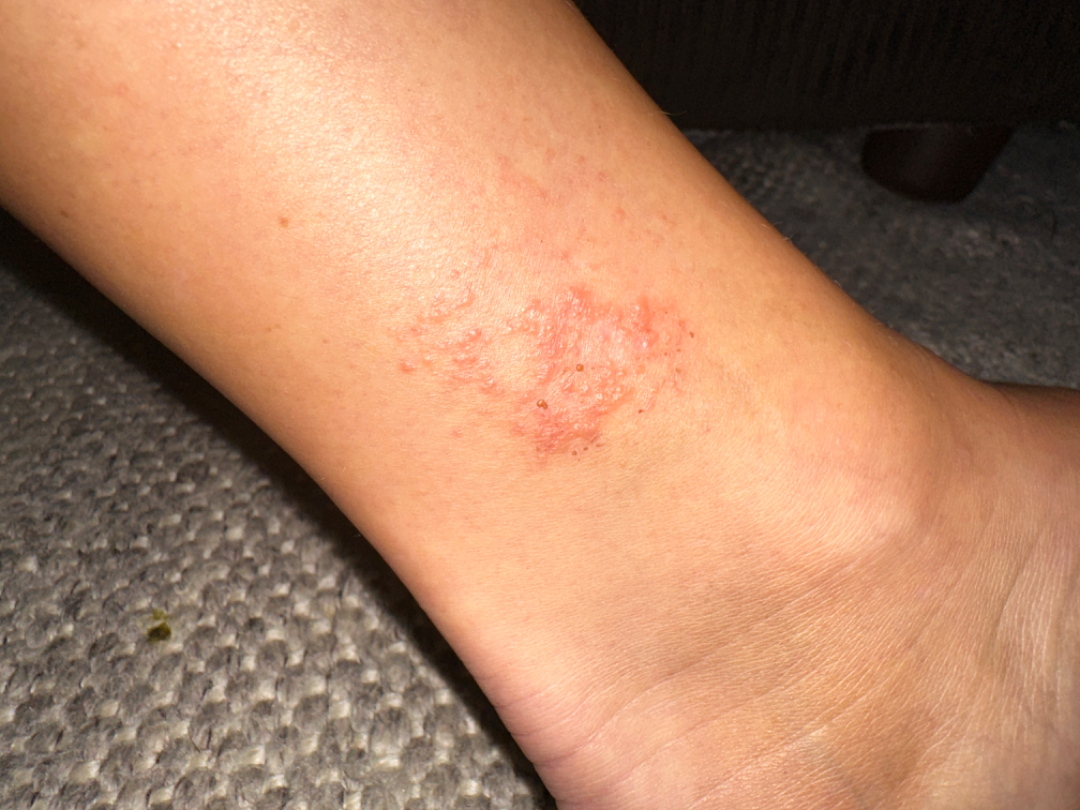The lesion is associated with bothersome appearance and itching.
No constitutional symptoms were reported.
The photograph was taken at an angle.
Skin tone: Fitzpatrick III; lay reviewers estimated Monk skin tone scale 3 or 5 (two reviewer pools disagreed).
Located on the leg.
The patient notes the lesion is raised or bumpy.
The patient notes the condition has been present for less than one week.
Eczema (most likely).